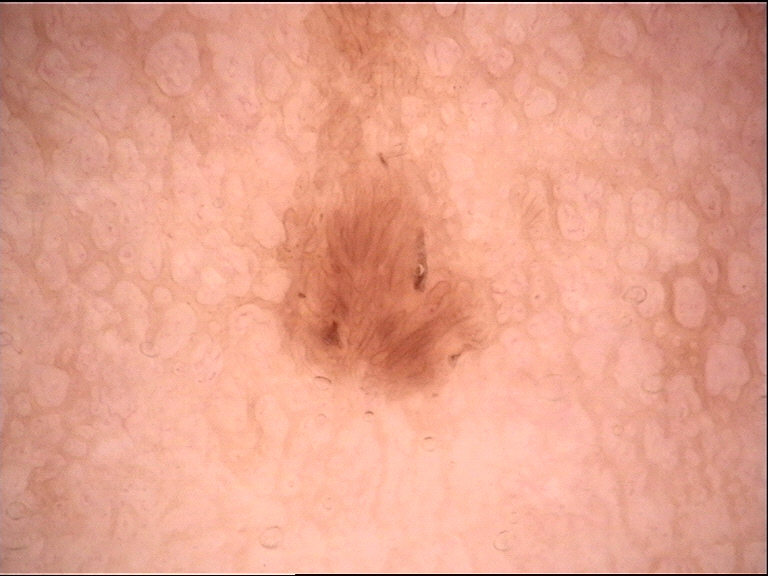– modality: dermatoscopy
– subtype: banal
– diagnostic label: dermal nevus (expert consensus)